A patient age 12:
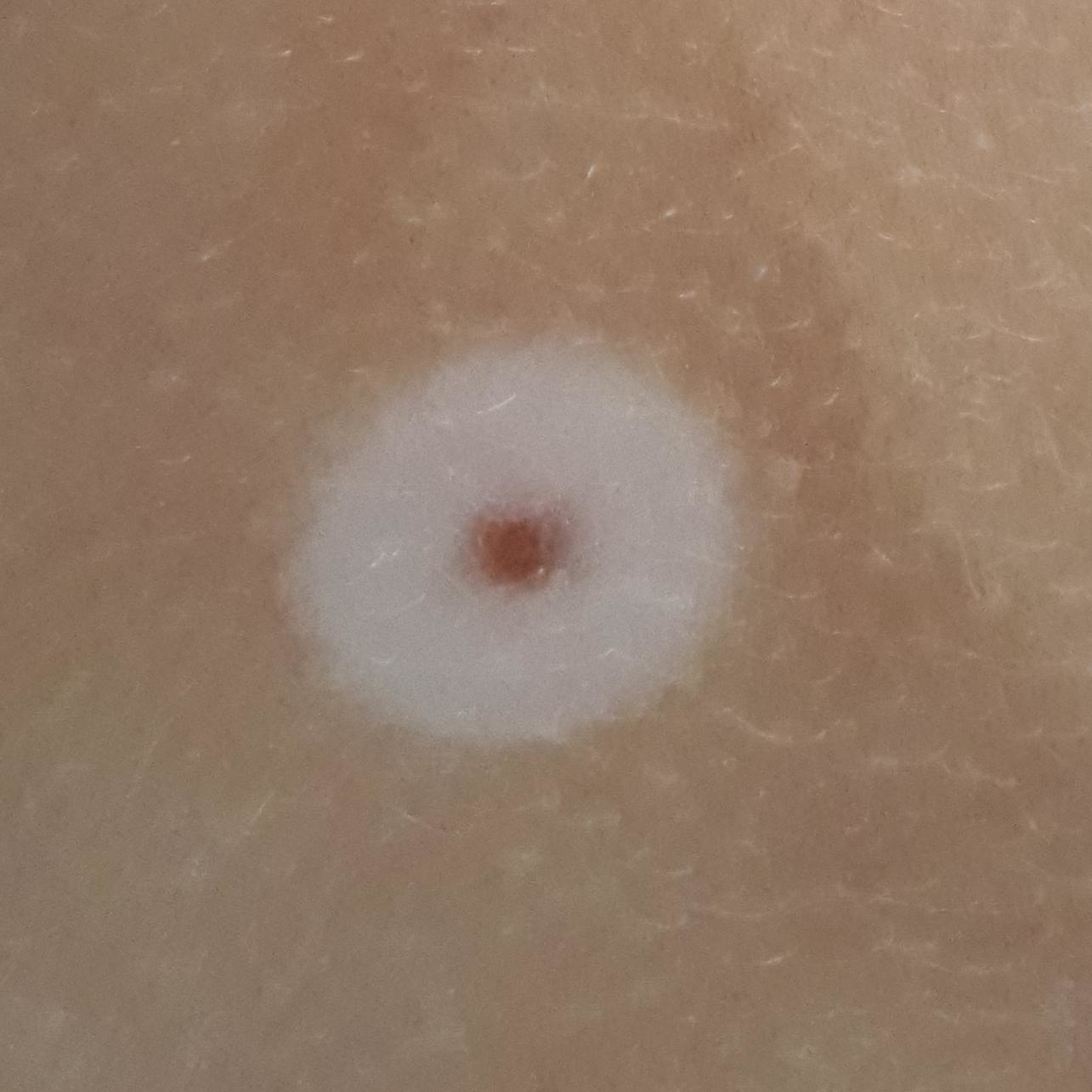Notes:
– site — the back
– patient-reported symptoms — none reported
– diagnostic label — nevus (clinical consensus)